The lesion involves the back of the hand, present for about one day, self-categorized by the patient as a rash, Fitzpatrick skin type II; human graders estimated Monk skin tone scale 3 or 5, the patient is male, the photograph was taken at an angle — 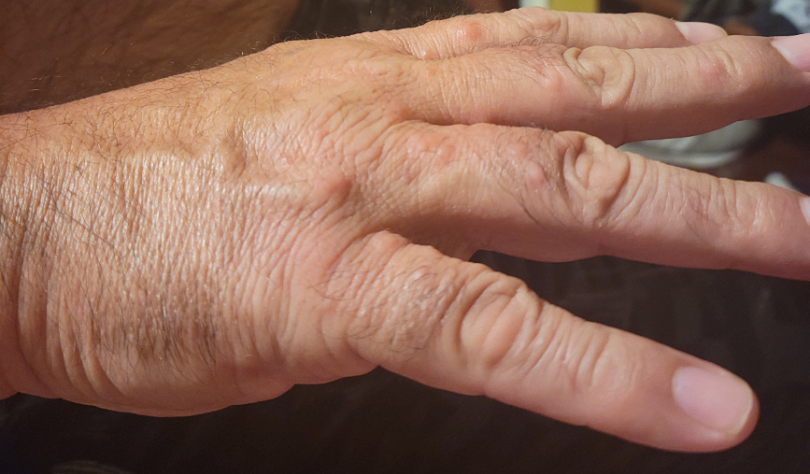clinical impression = the differential includes Histiocytosis of skin and Insect Bite, with no clear leading consideration; an alternative is Lichenoid myxedema